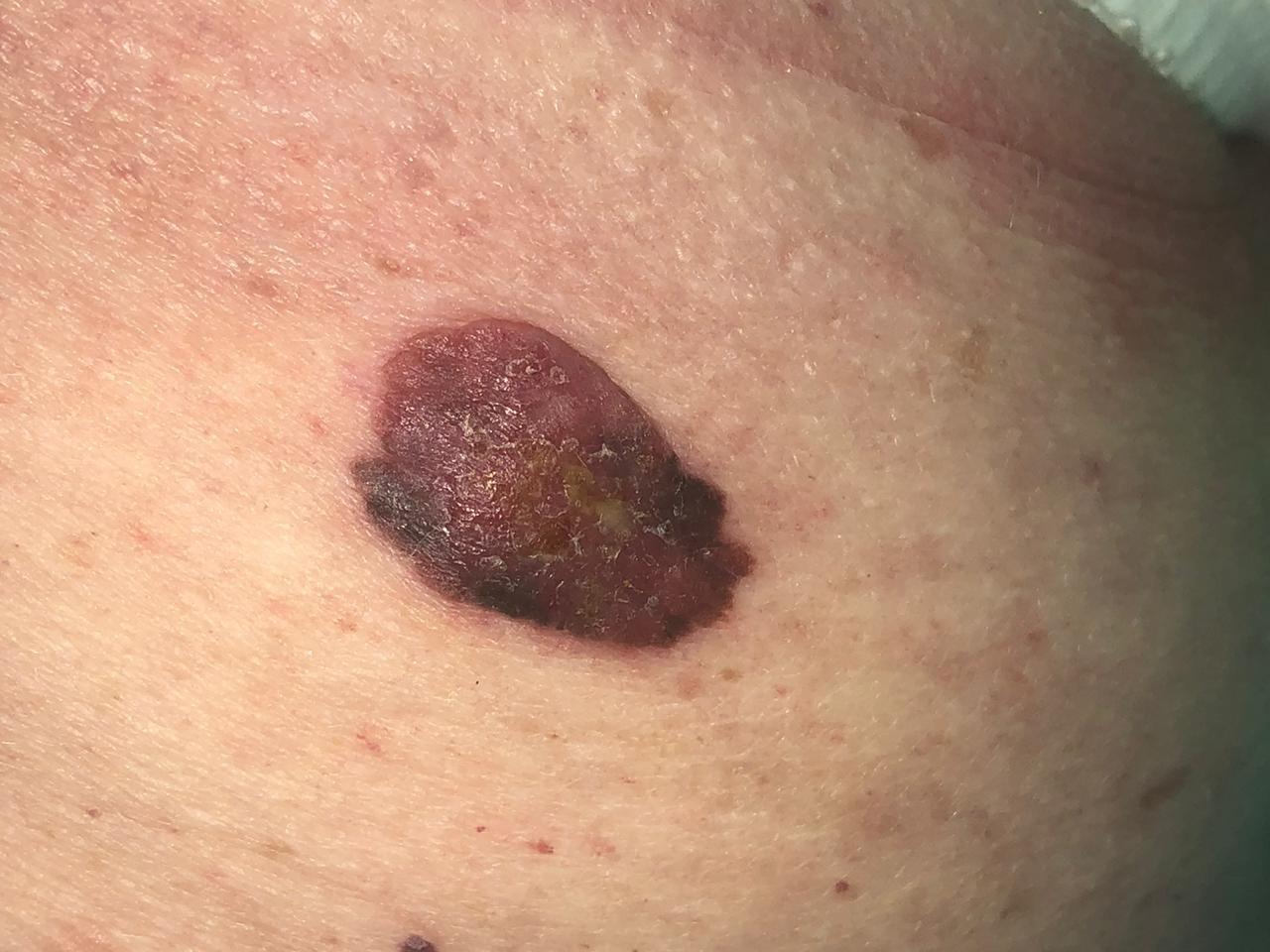body site: a lower extremity | pathology: Melanoma (biopsy-proven).